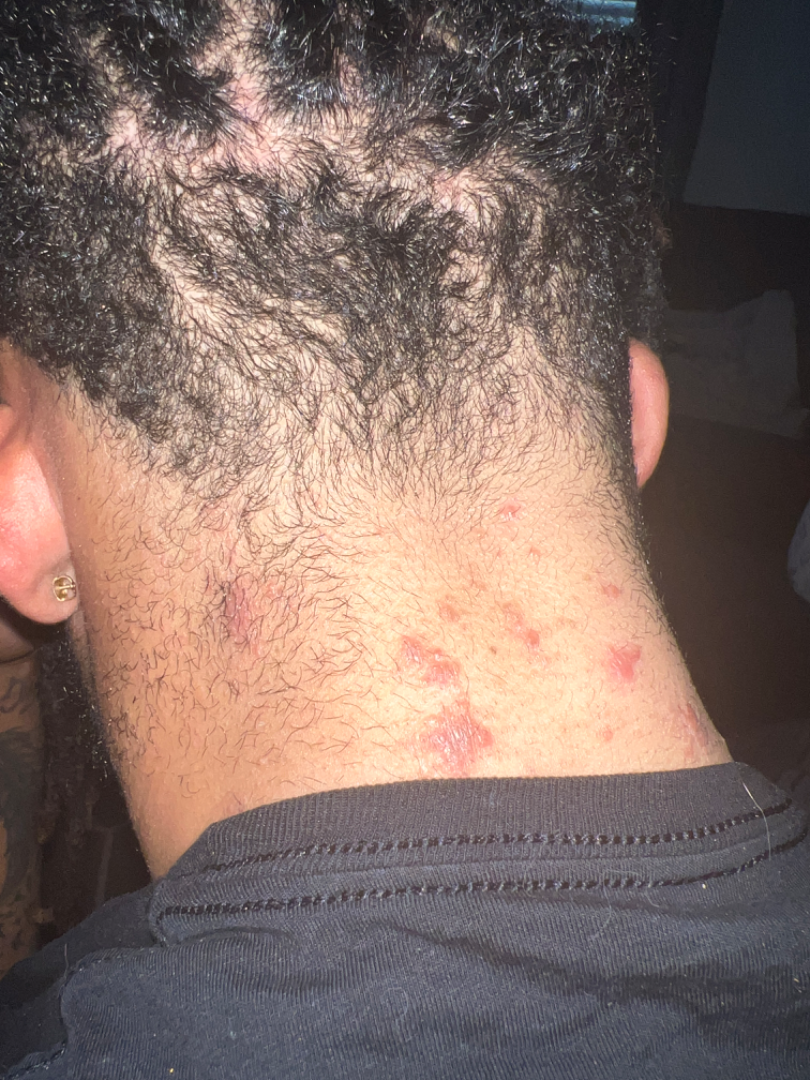Q: What was the assessment?
A: ungradable on photographic review
Q: How was the photo taken?
A: close-up
Q: Anatomic location?
A: head or neck
Q: What is the patient's skin tone?
A: Fitzpatrick phototype V; human graders estimated Monk skin tone scale 4 (US pool) or 3 (India pool)
Q: What symptoms does the patient report?
A: itching, pain, burning and bothersome appearance
Q: What is the lesion texture?
A: raised or bumpy and fluid-filled
Q: How does the patient describe it?
A: a rash
Q: Constitutional symptoms?
A: none reported
Q: When did this start?
A: one to four weeks